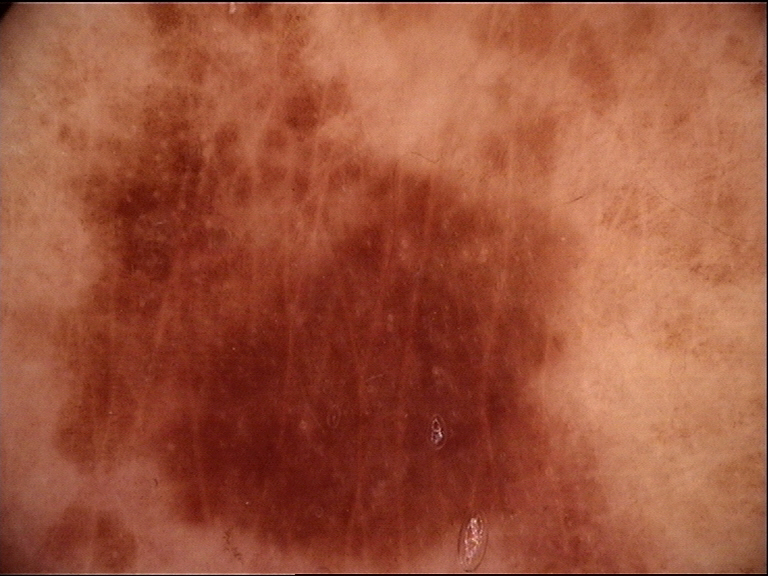Diagnosed as a benign lesion — a dysplastic junctional nevus.